This is a dermoscopic photograph of a skin lesion: 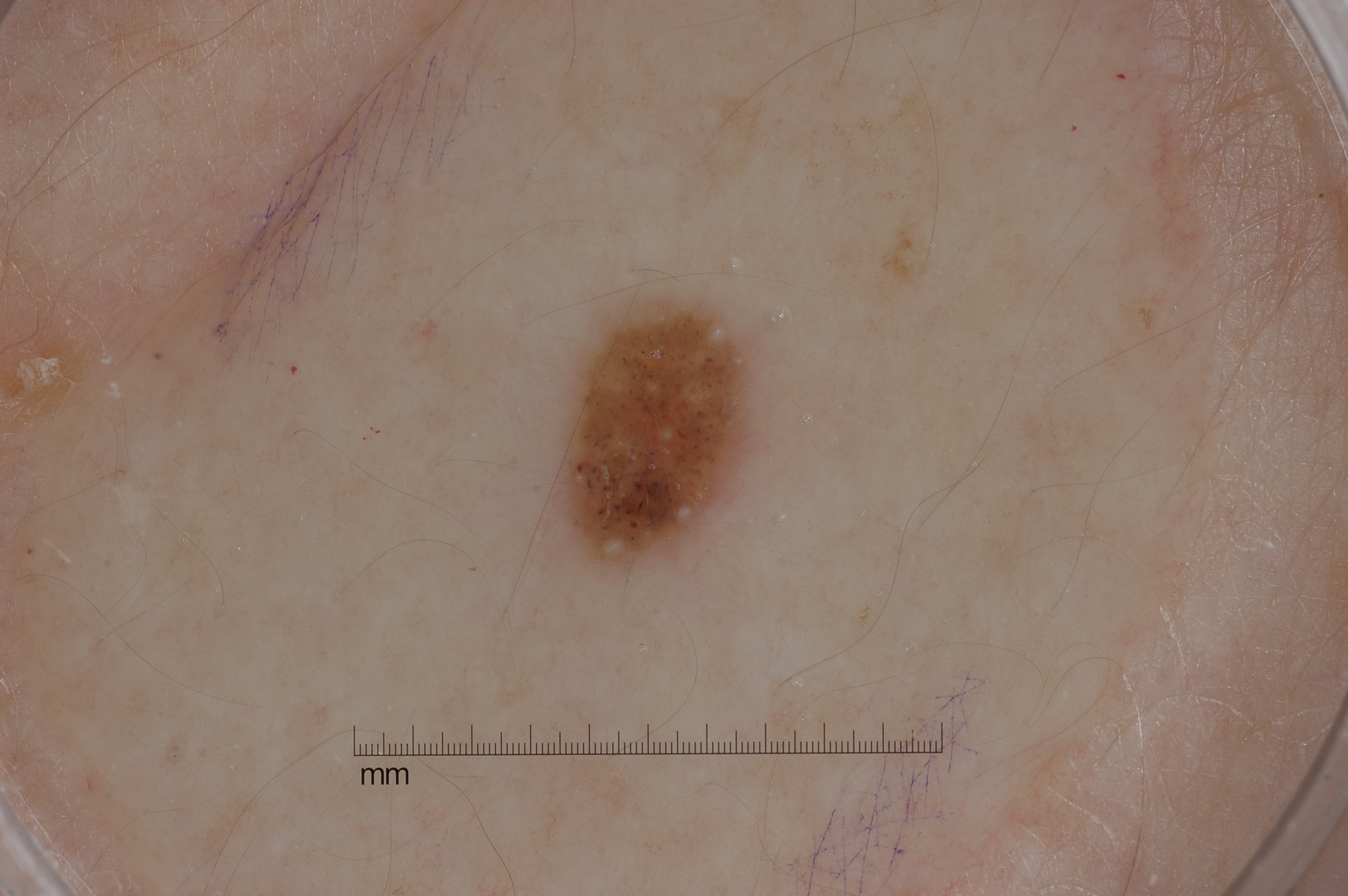Case summary: The dermoscopic pattern shows milia-like cysts, with no negative network, streaks, or pigment network. The lesion's extent is x1=569, y1=301, x2=747, y2=567. The lesion is small relative to the field of view. Conclusion: Expert review diagnosed this as a seborrheic keratosis, a benign skin lesion.